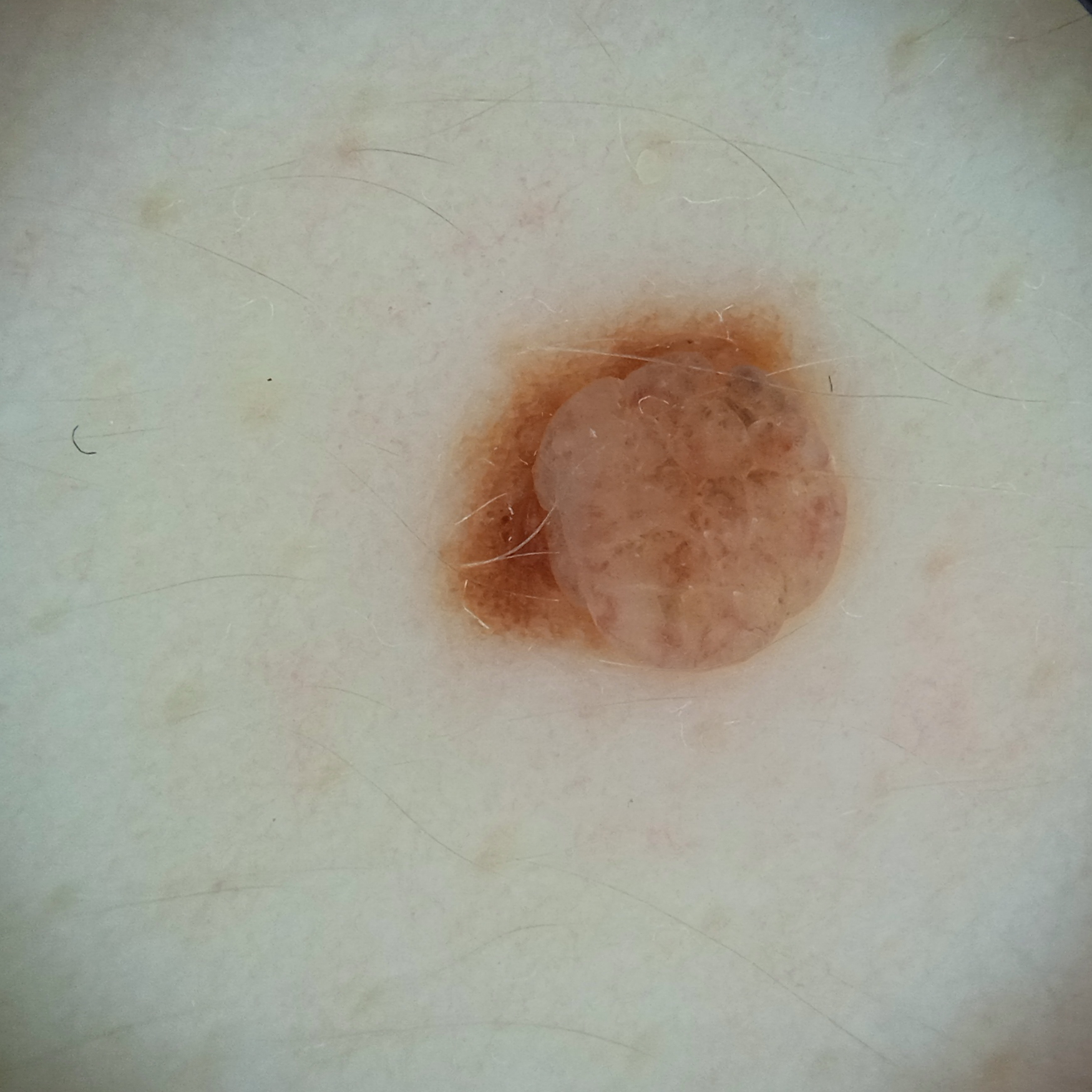– nevus count: numerous melanocytic nevi
– modality: dermoscopy
– sun reaction: skin reddens with sun exposure
– anatomic site: the back
– size: 4.5 mm
– assessment: melanocytic nevus (dermatologist consensus)